Contact-polarized dermoscopy of a skin lesion. The chart documents melanoma in a first-degree relative but no prior melanoma.
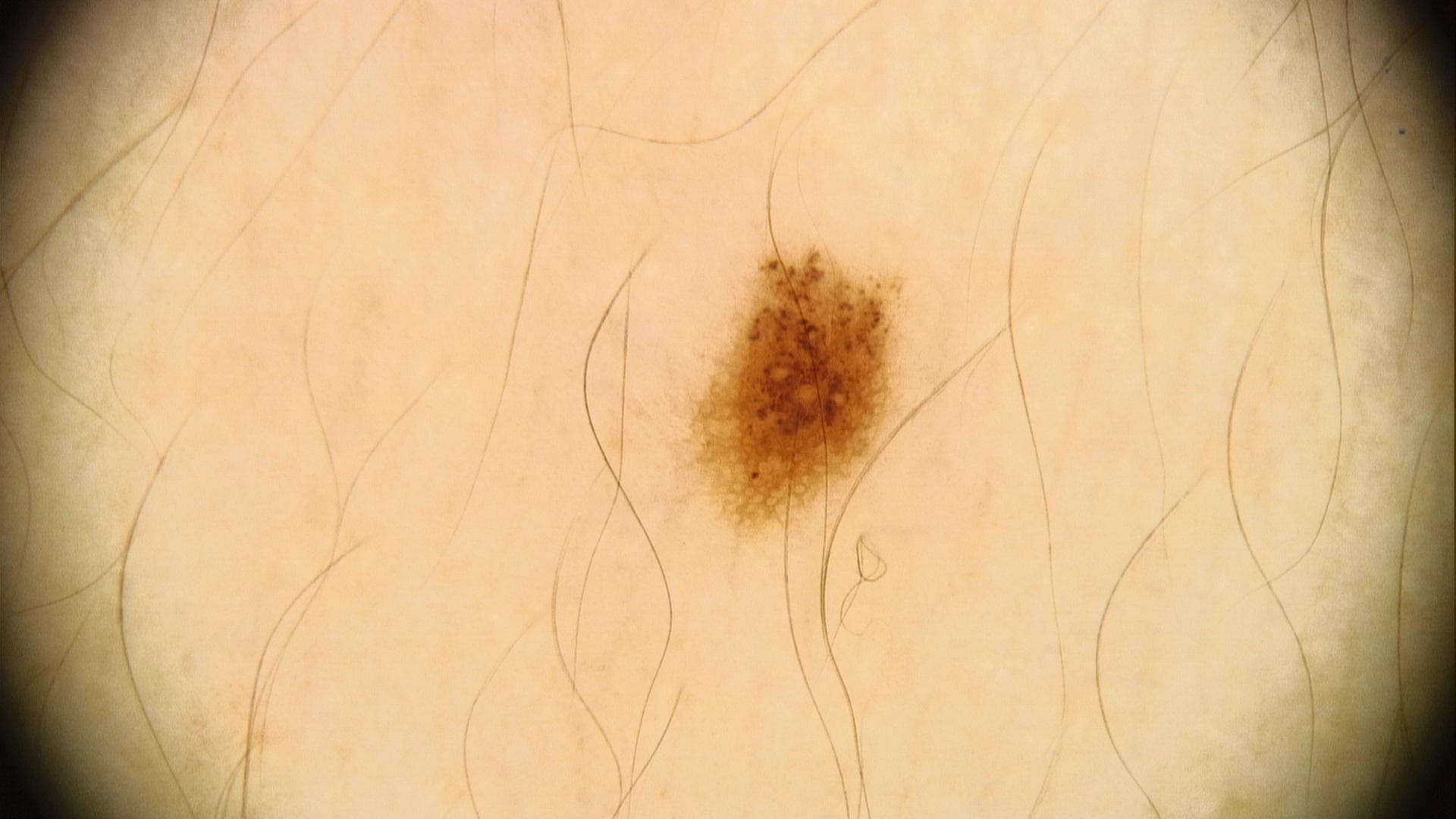Impression: Expert review favored a benign lesion — a nevus.